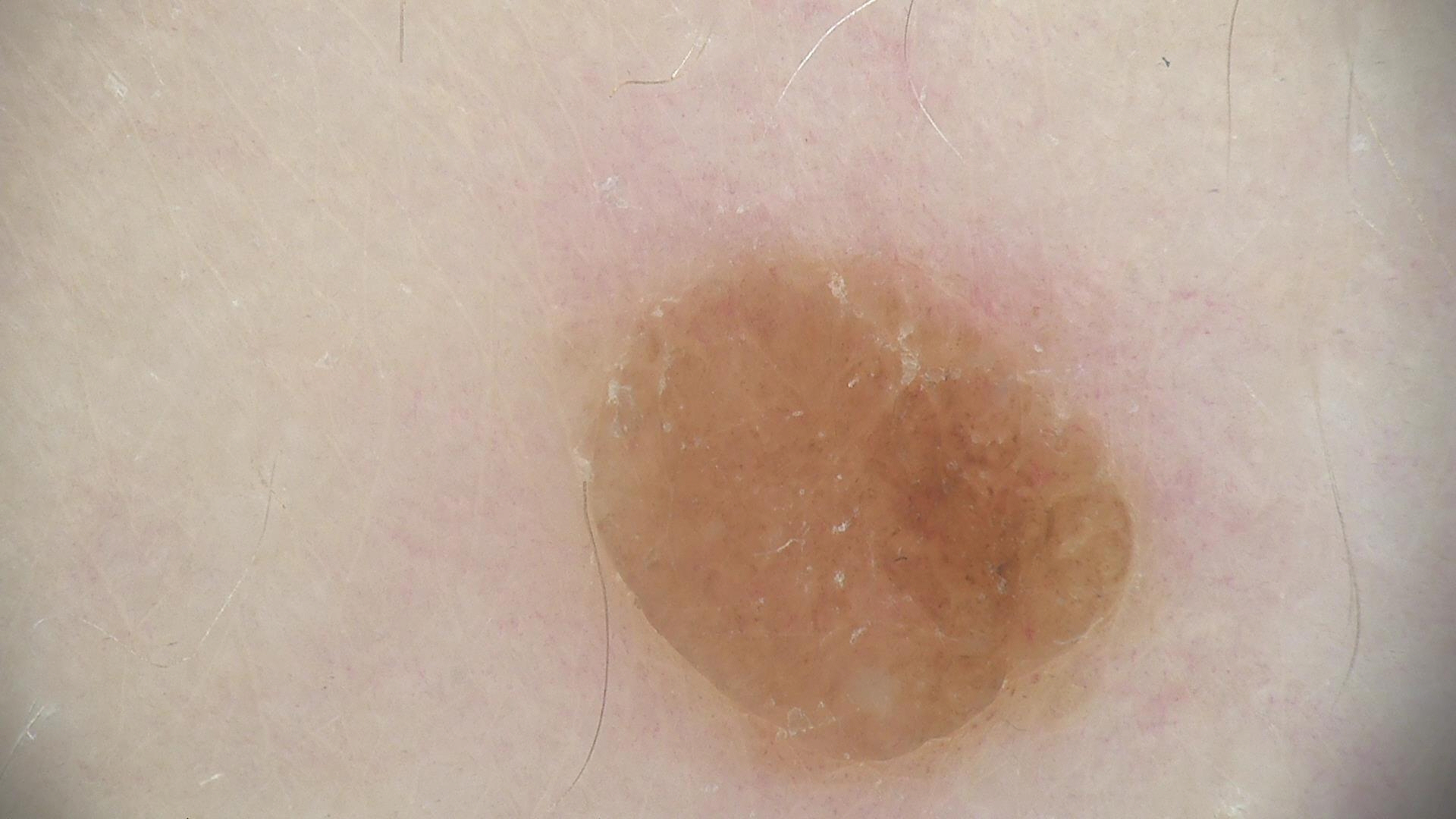A dermoscopy image of a single skin lesion.
Labeled as a banal lesion — a dermal nevus.